This is a close-up image · located on the arm and head or neck:
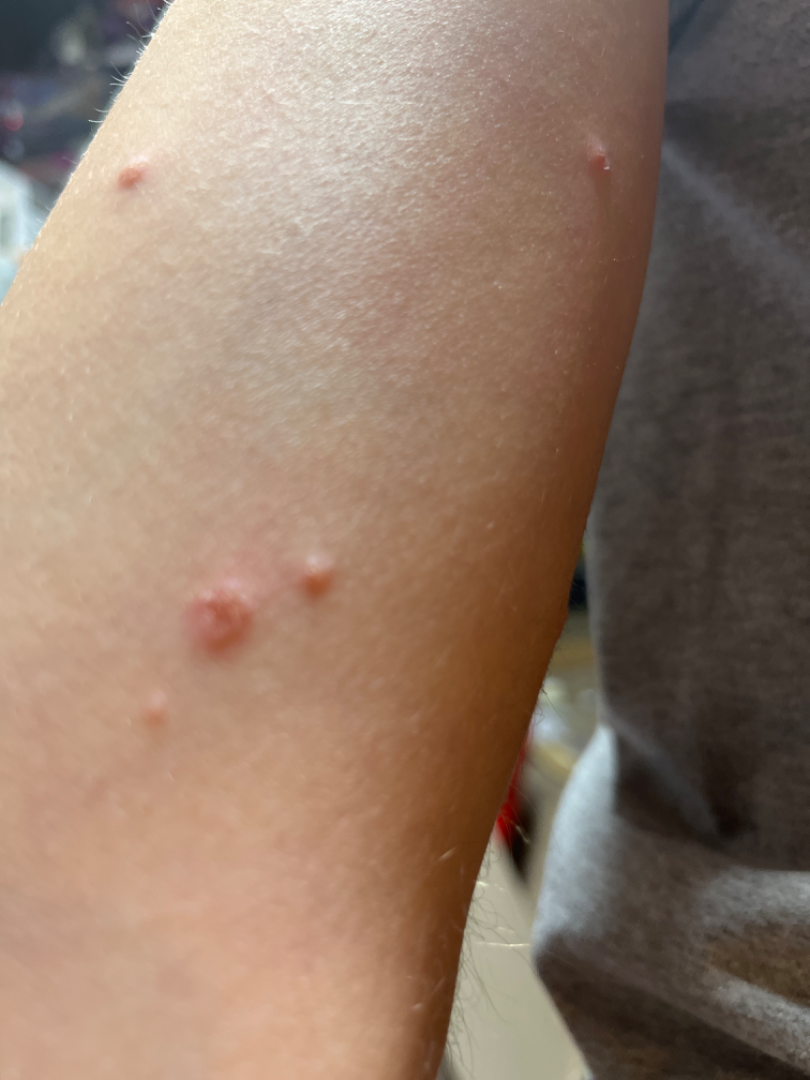Background: Texture is reported as raised or bumpy and fluid-filled. No constitutional symptoms were reported. The lesion is associated with itching and bothersome appearance. The condition has been present for less than one week. Findings: Consistent with Psoriasis.